A skin lesion imaged with a dermatoscope: 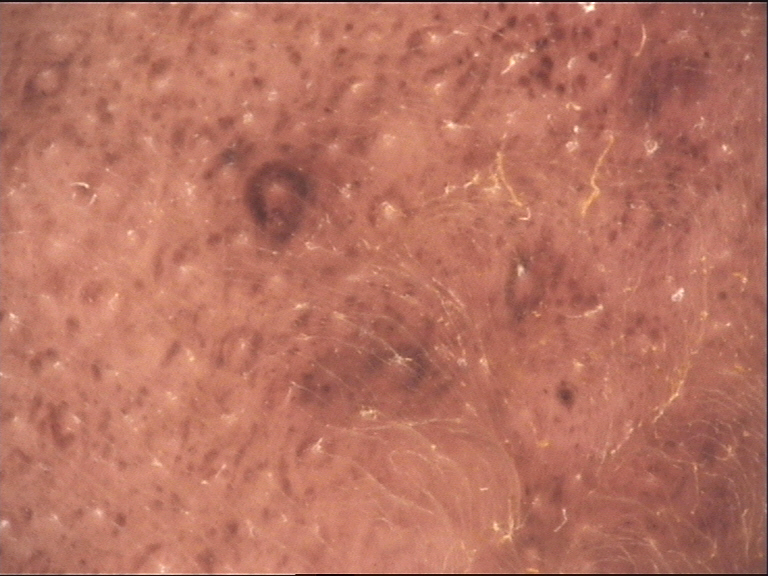subtype: banal | assessment: congenital compound nevus (expert consensus).